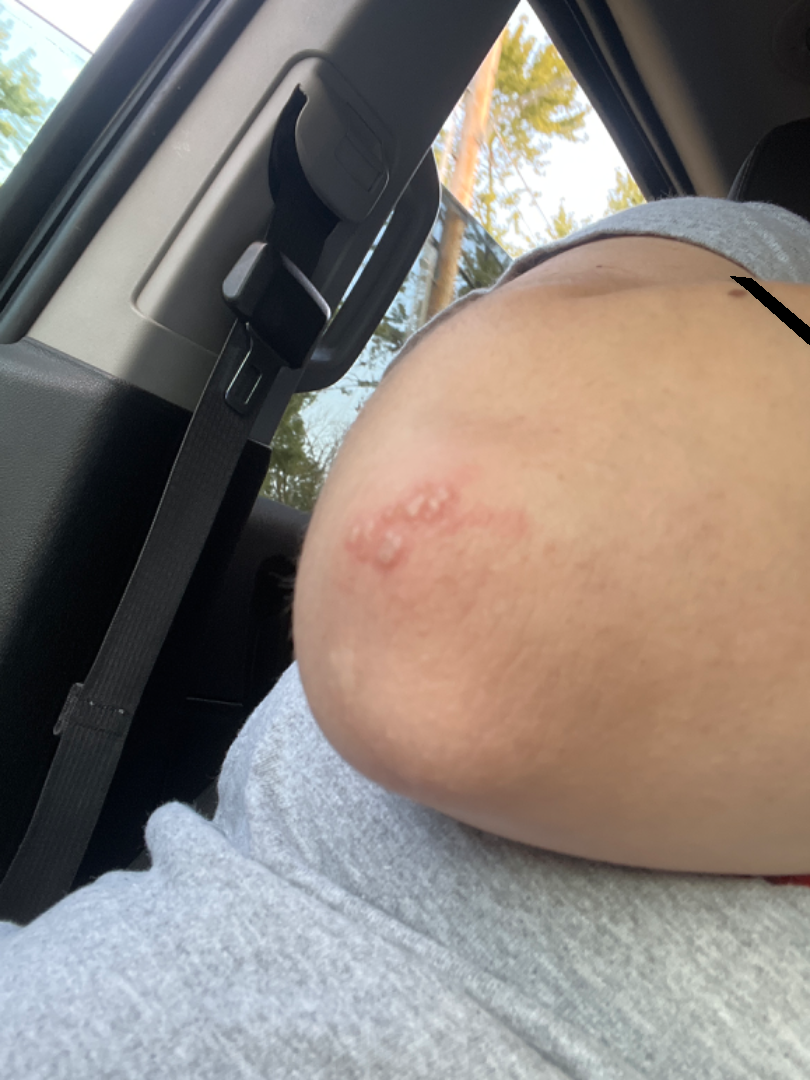The patient indicates enlargement, itching, burning and pain. Associated systemic symptoms include fatigue and fever. The lesion is described as fluid-filled and raised or bumpy. The condition has been present for less than one week. This image was taken at an angle. Self-categorized by the patient as skin that appeared healthy to them. On teledermatology review: Herpes Simplex (primary); Impetigo (considered); Herpes Zoster (considered).